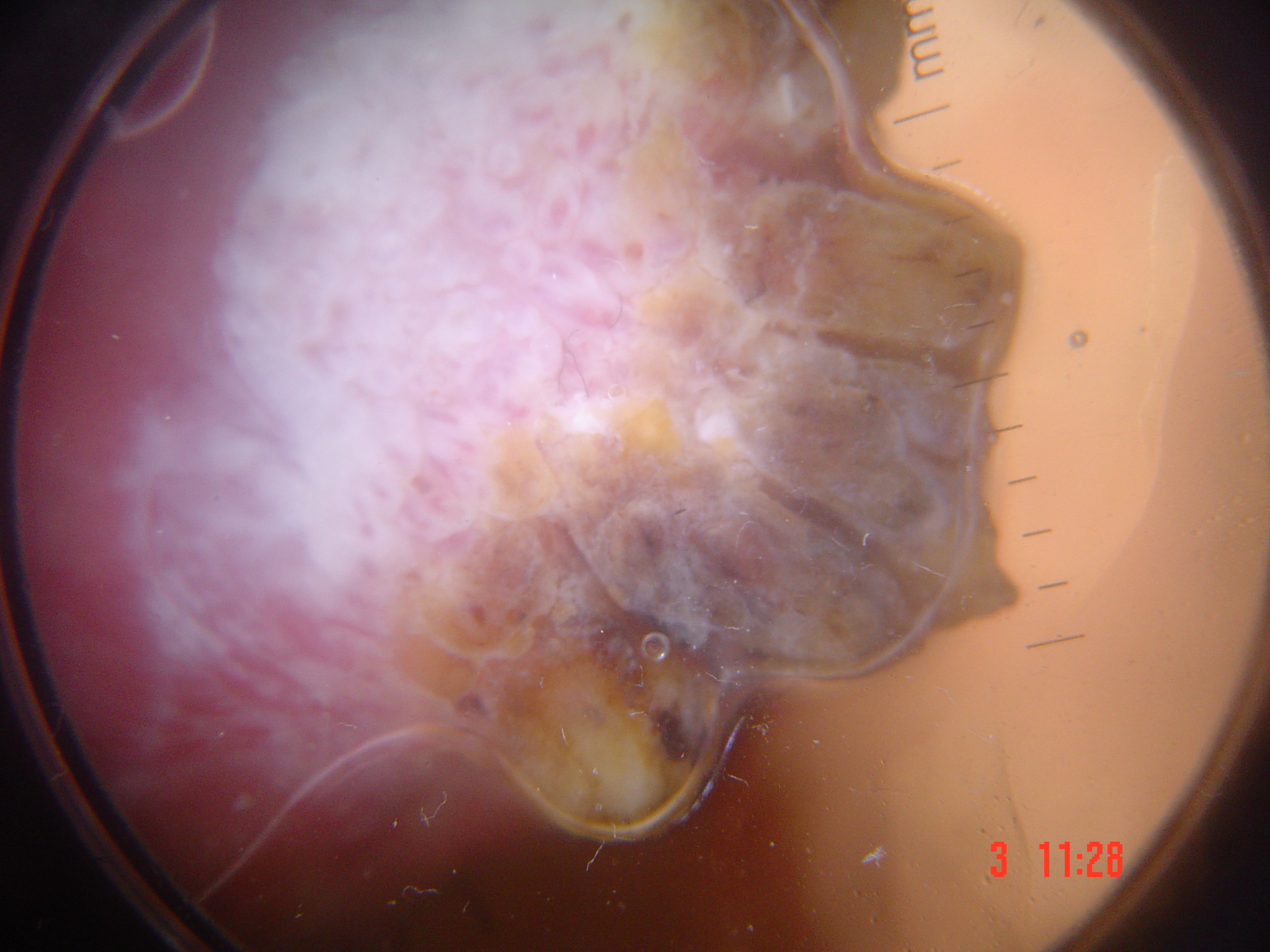* pathology: squamous cell carcinoma (biopsy-proven)